The patient considered this a rash. The contributor reports the condition has been present for less than one week. The patient is a male aged 40–49. The contributor reports itching and bothersome appearance. The photograph was taken at a distance. Texture is reported as raised or bumpy. Located on the leg. The patient reported no systemic symptoms — 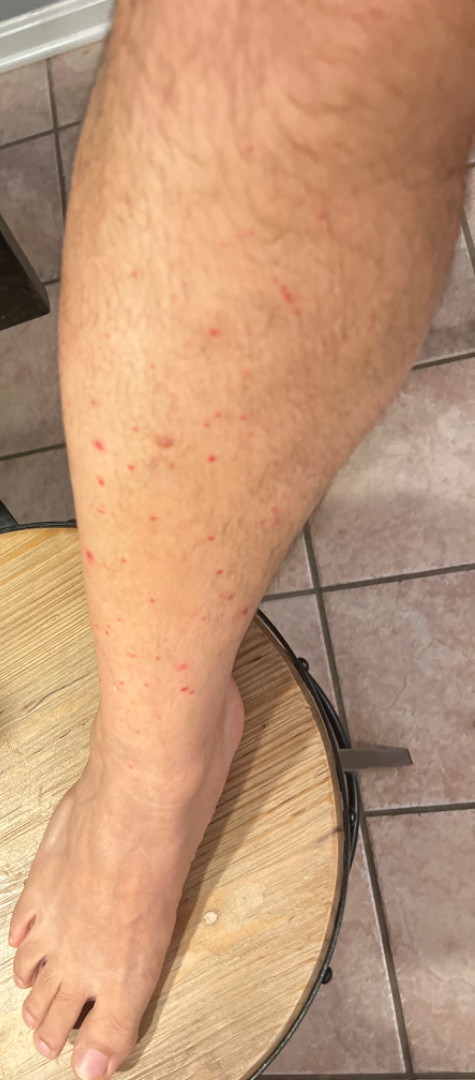clinical impression: the favored diagnosis is Leukocytoclastic Vasculitis; a remote consideration is Drug Rash; less likely is Scabies; less probable is Insect Bite; lower on the differential is Pigmented purpuric eruption